Located on the head or neck and arm · female subject, age 30–39 · the photograph is a close-up of the affected area:
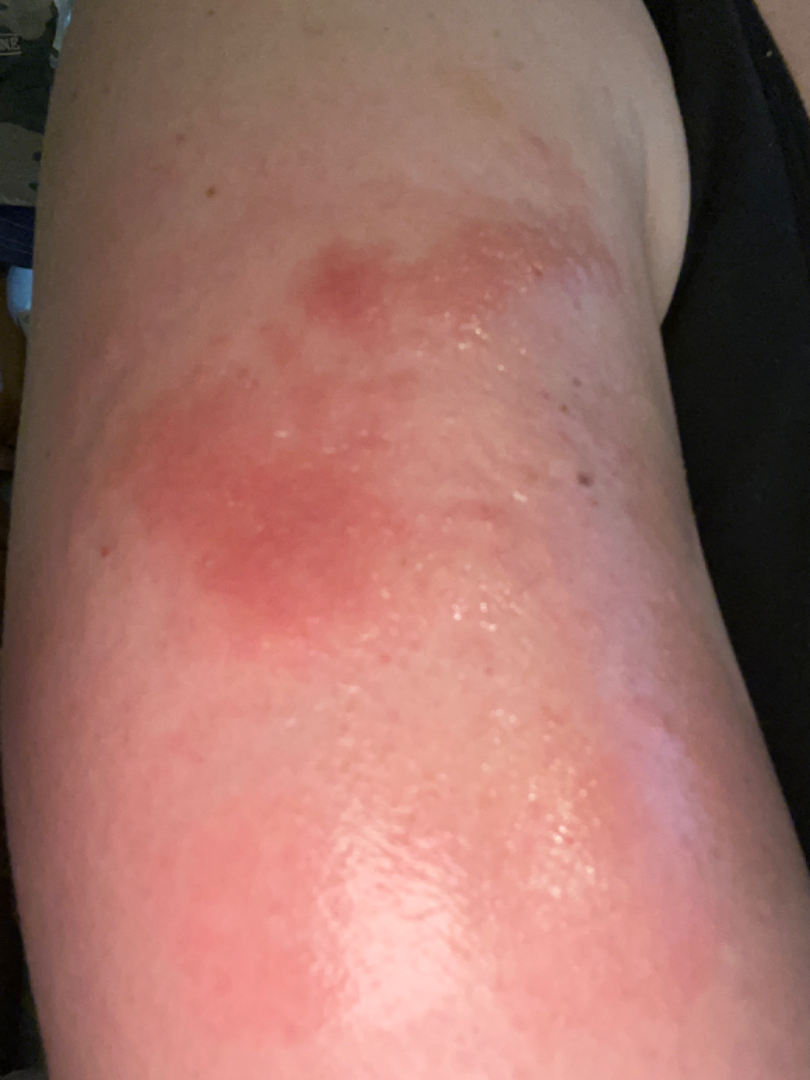Notes:
– assessment — not assessable